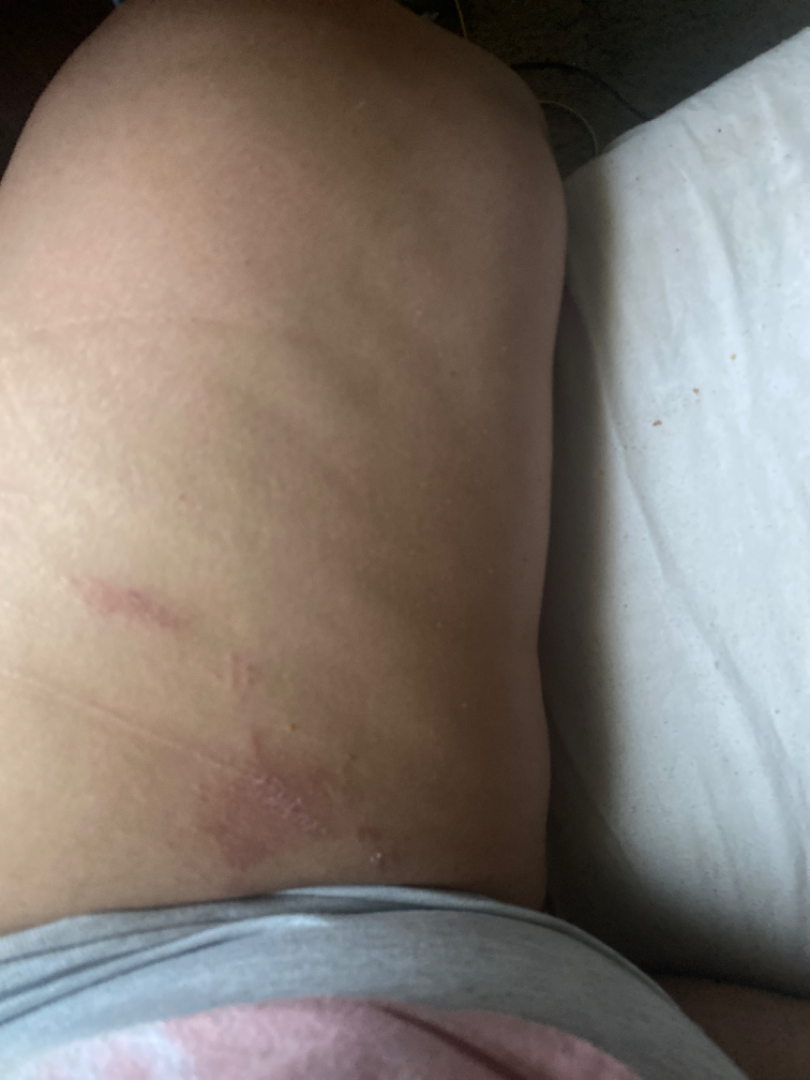Impression: The reviewer was unable to grade this case for skin condition. History: Reported lesion symptoms include burning, itching and pain. An image taken at a distance. The affected area is the leg, front of the torso and top or side of the foot. The patient described the issue as a rash. Texture is reported as rough or flaky.